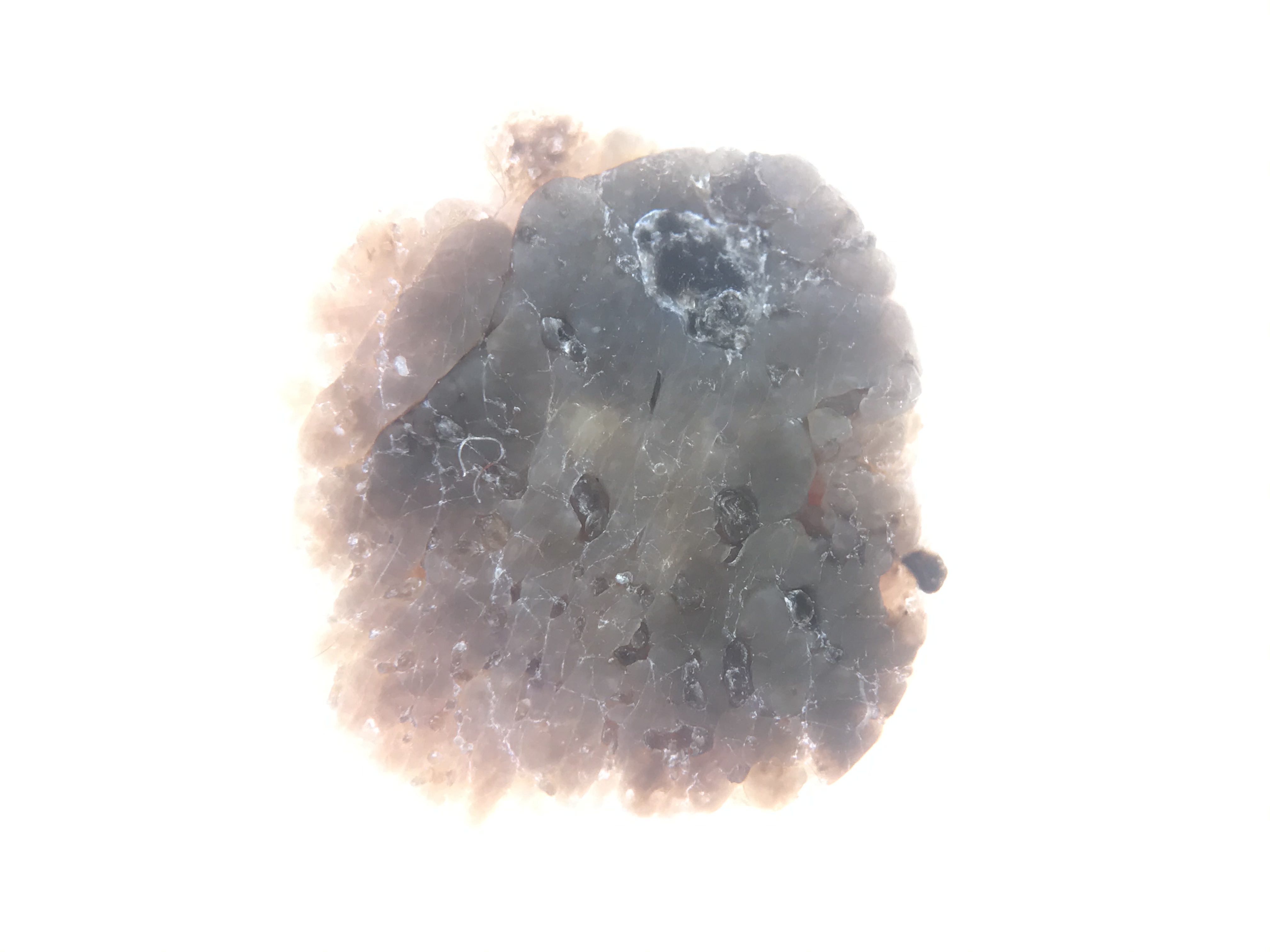A dermoscopy image of a single skin lesion. Consistent with a keratinocytic lesion — a seborrheic keratosis.